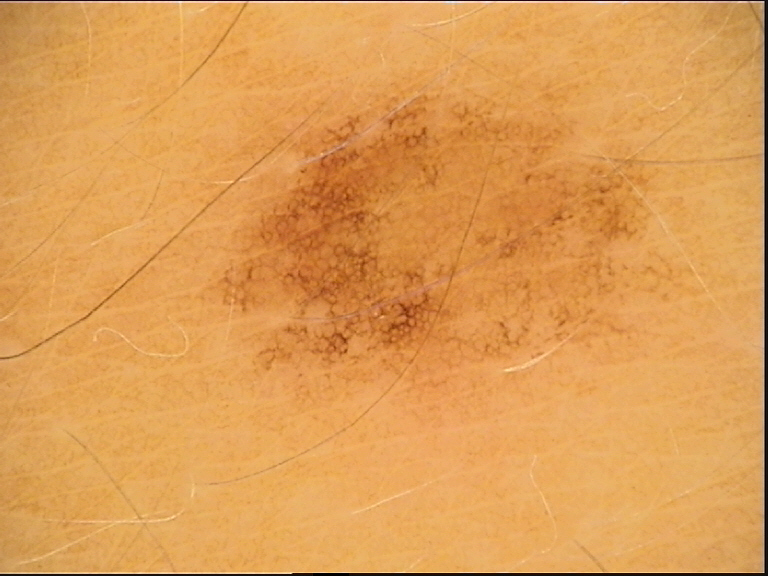Q: What kind of image is this?
A: dermoscopy
Q: What is the diagnosis?
A: dysplastic junctional nevus (expert consensus)